The lesion is associated with burning, itching, darkening and pain; the contributor is 30–39, female; texture is reported as fluid-filled and raised or bumpy; self-categorized by the patient as a rash; the patient reports the condition has been present for since childhood; the photograph was taken at a distance; the head or neck, palm, arm and leg are involved; the patient reports associated joint pain, chills and shortness of breath:
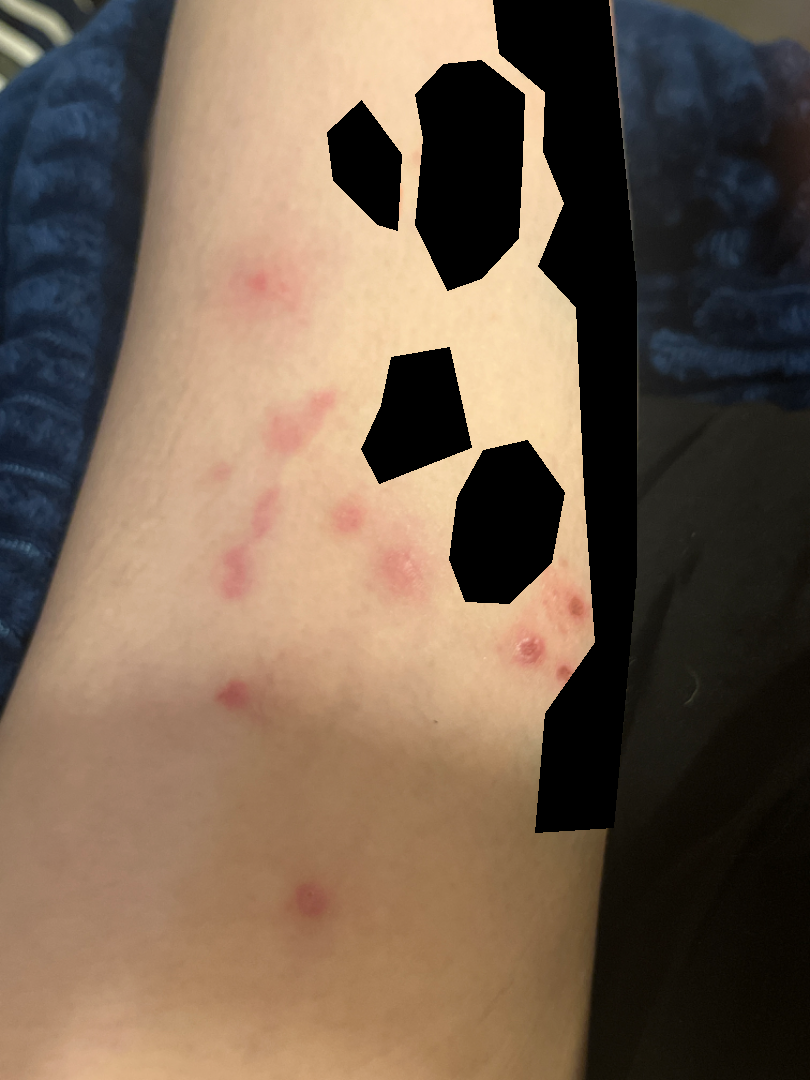Q: What is the dermatologist's impression?
A: most consistent with Prurigo nodularis; also raised was Folliculitis